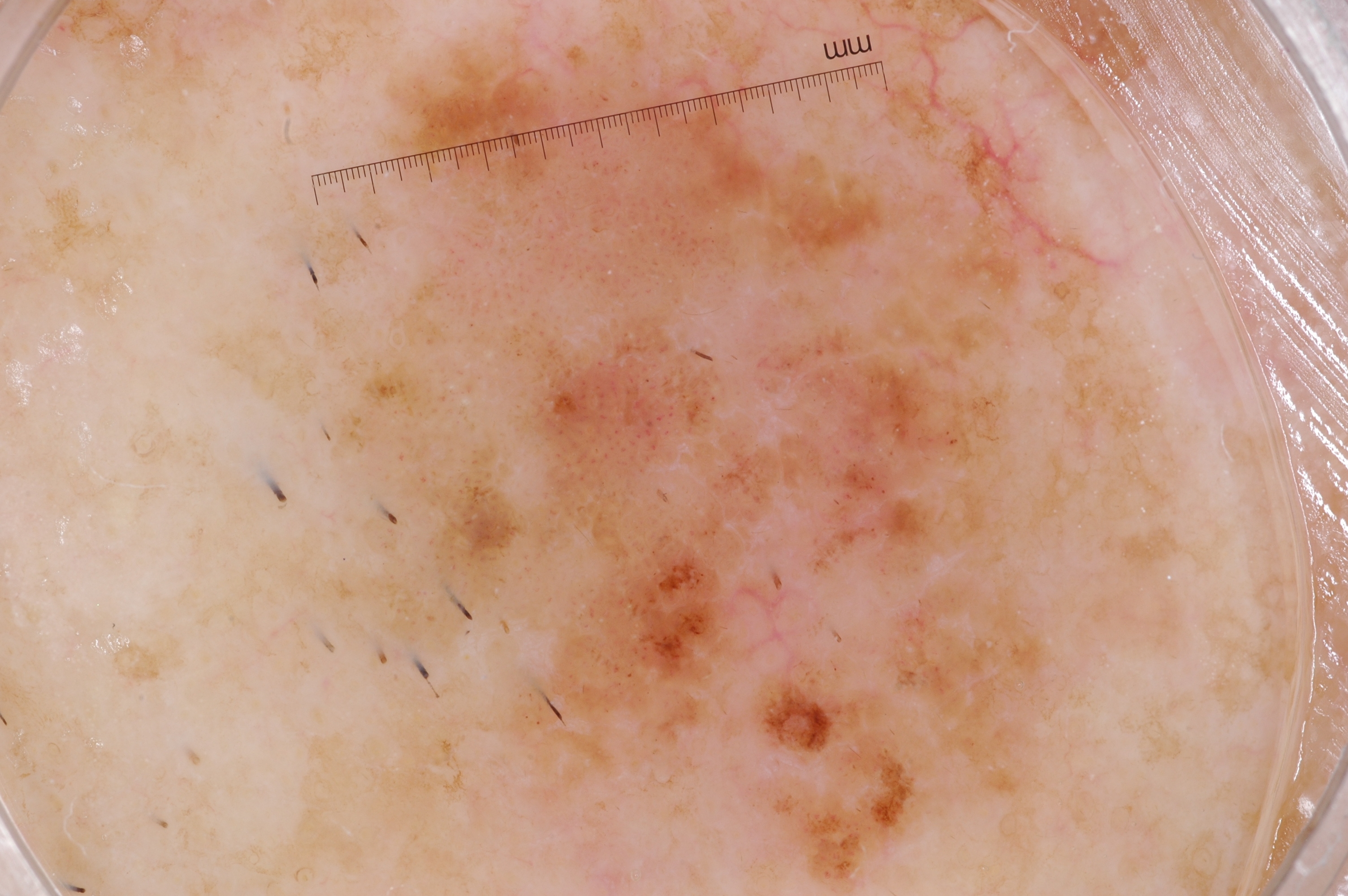A male subject aged around 80.
A dermatoscopic image of a skin lesion.
With coordinates (x1, y1, x2, y2), lesion location: [225, 2, 1081, 895].
Dermoscopic review identifies milia-like cysts.
Consistent with a seborrheic keratosis, a benign lesion.